A female patient about 35 years old. A skin lesion imaged with contact-polarized dermoscopy.
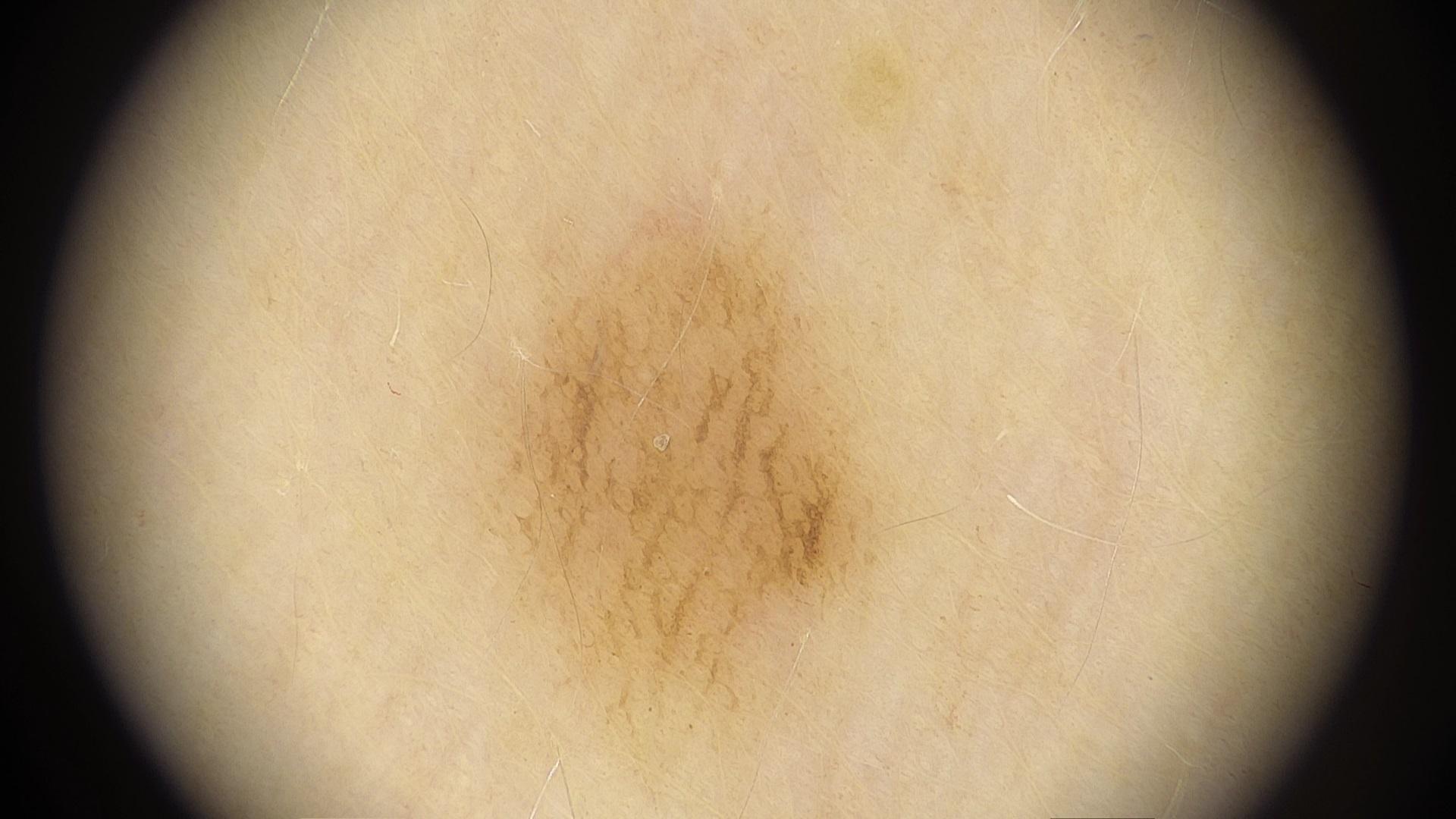The lesion was found on the trunk.
The diagnostic impression was a nevus.